The affected area is the leg; the photograph is a close-up of the affected area:
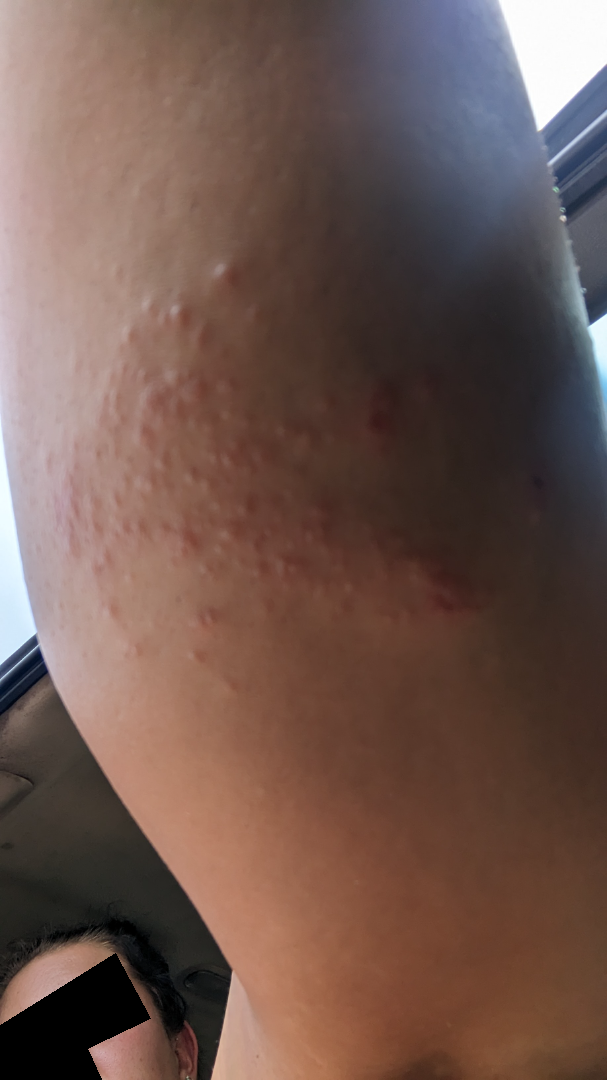Impression: The reviewer was unable to grade this case for skin condition.